A dermoscopy image of a single skin lesion: 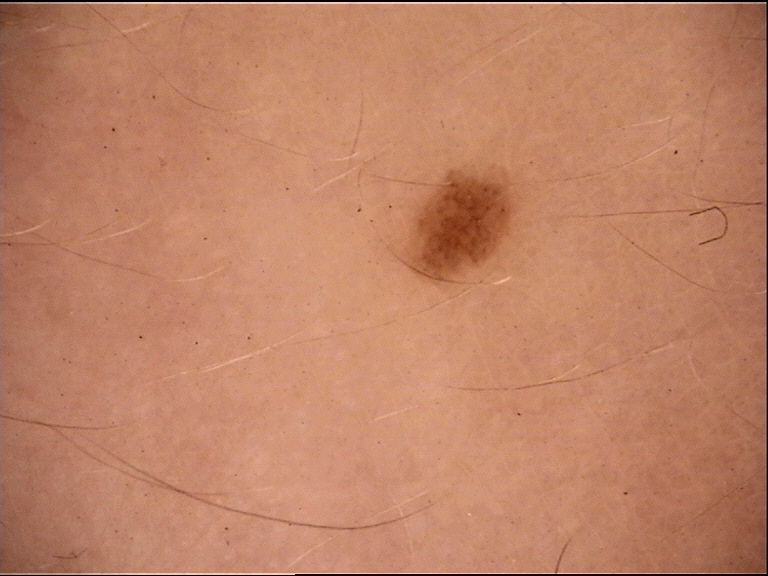Conclusion:
Consistent with a junctional nevus.